The patient notes the lesion is raised or bumpy, the lesion involves the front of the torso, present for about one day, the patient notes itching, the photograph was taken at an angle, the patient considered this a rash.
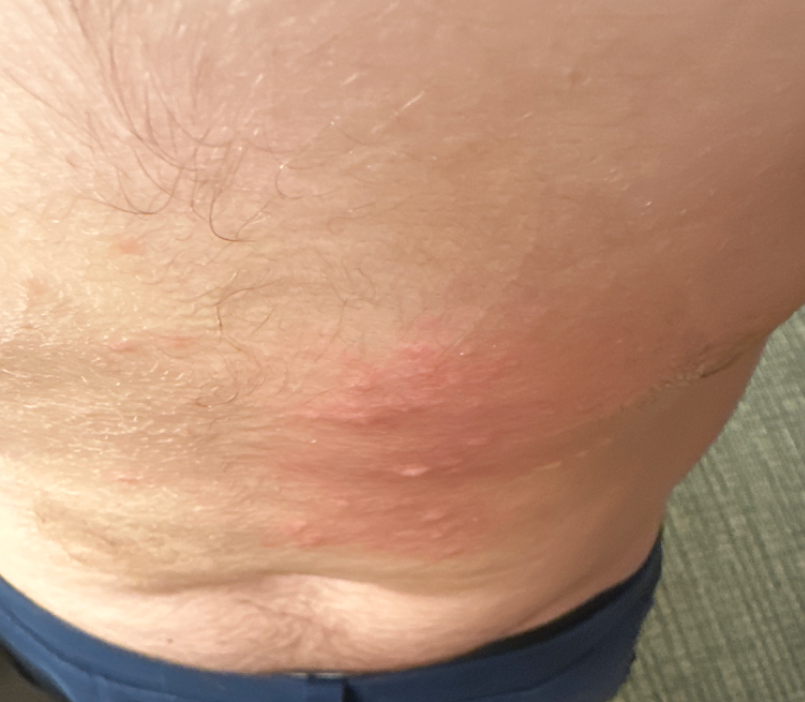On photographic review, Urticaria (most likely); Acute dermatitis, NOS (considered).